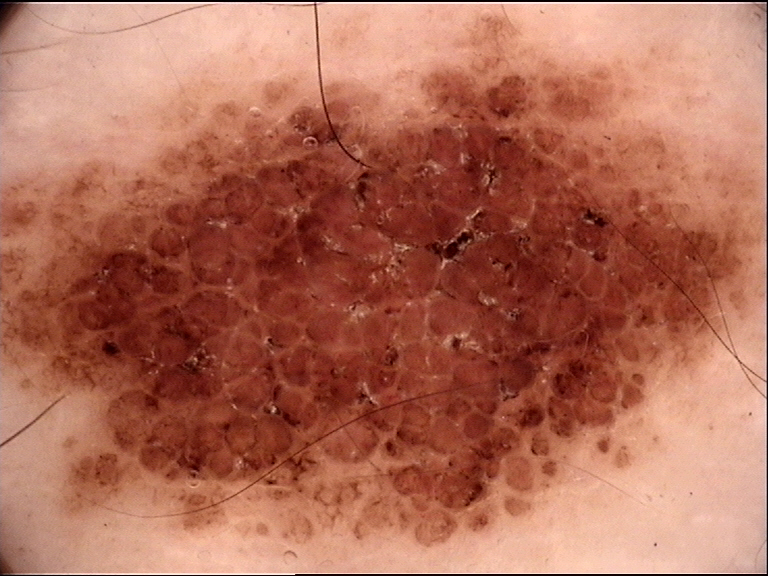The diagnosis was a dysplastic compound nevus.